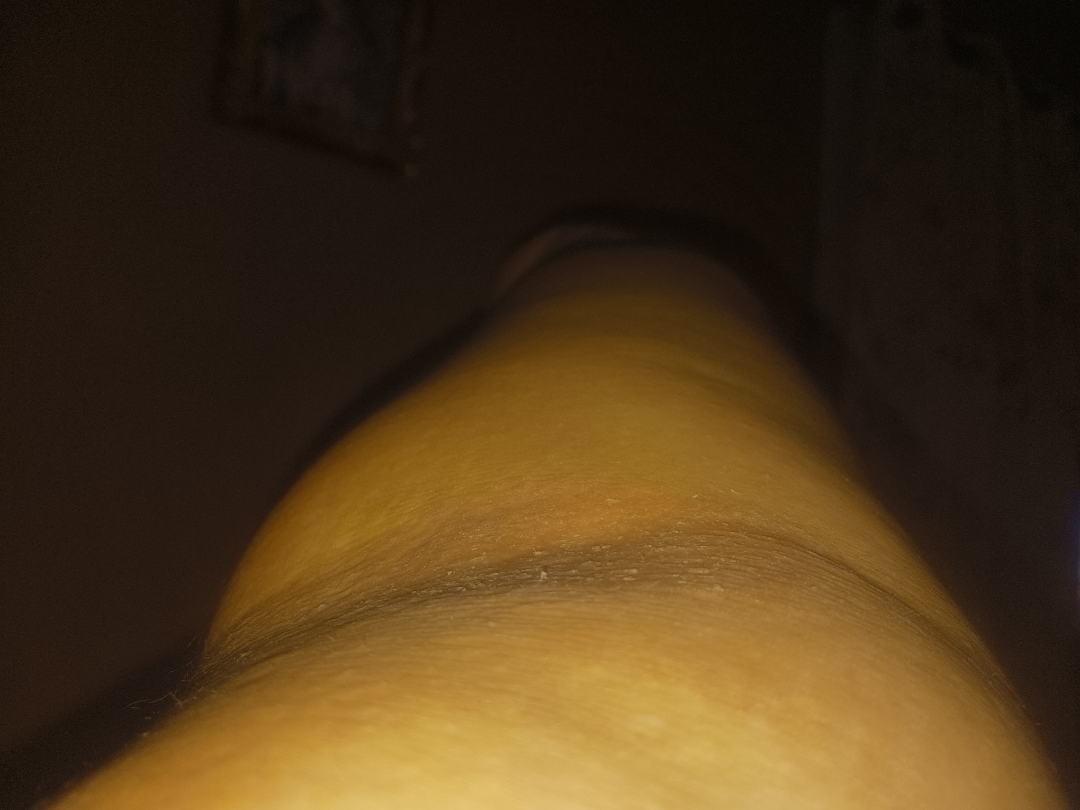Q: What was the assessment?
A: unable to determine
Q: Patient demographics?
A: female, age 40–49
Q: How was the photo taken?
A: at an angle
Q: Anatomic location?
A: arm